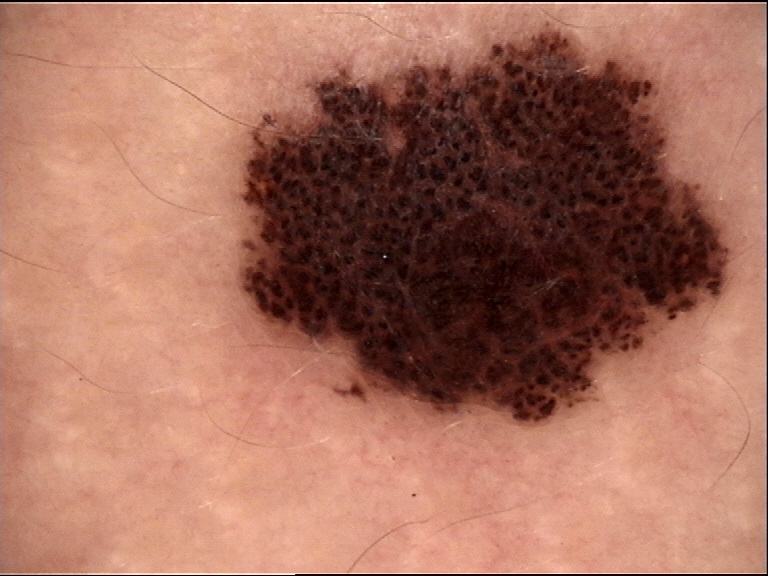Case: Dermoscopy of a skin lesion. Conclusion: Consistent with a dysplastic junctional nevus.